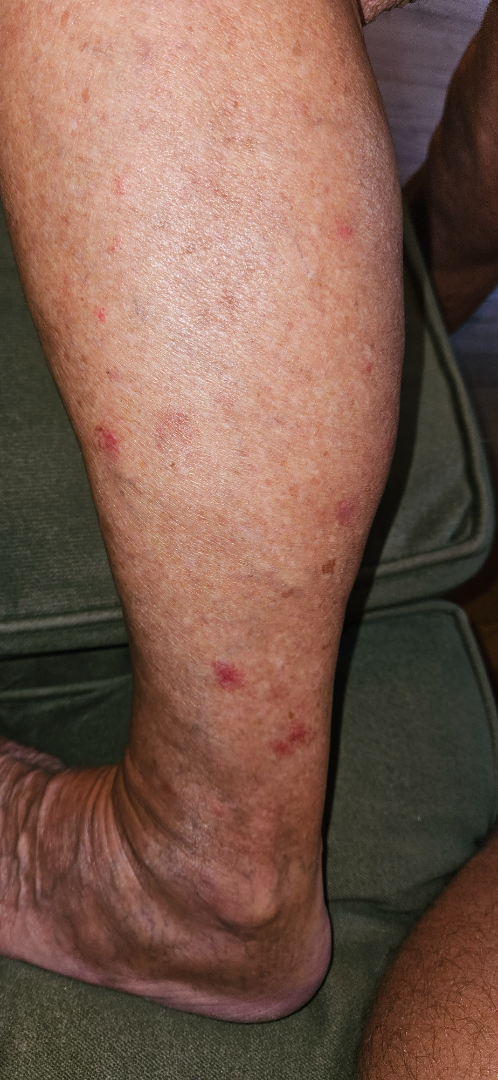<summary>
<differential>
  <tied_lead>Insect Bite, Eczema, Leukocytoclastic Vasculitis</tied_lead>
</differential>
</summary>